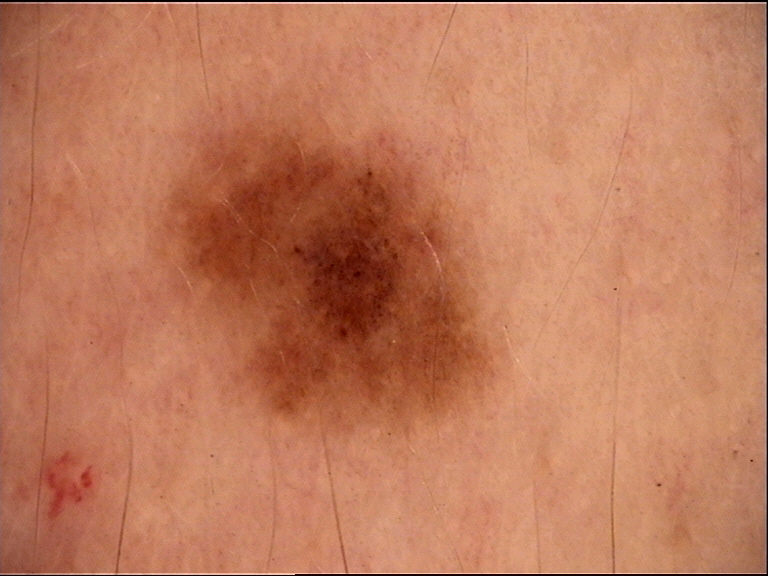diagnostic label: dysplastic junctional nevus (expert consensus)